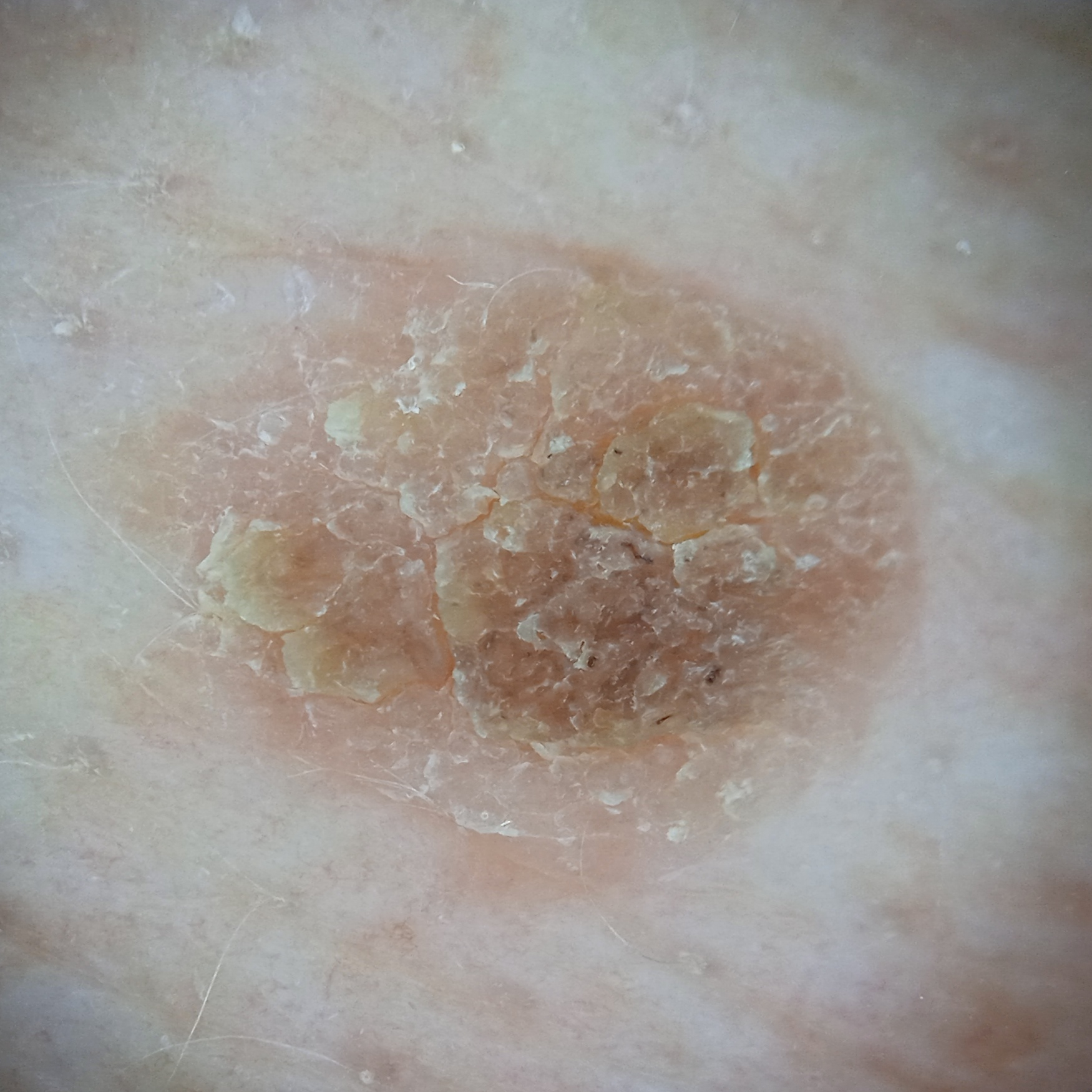Q: Tell me about the patient.
A: female, aged 73
Q: Where is the lesion?
A: the back
Q: Lesion size?
A: 8.6 mm
Q: What was the diagnosis?
A: seborrheic keratosis (dermatologist consensus)